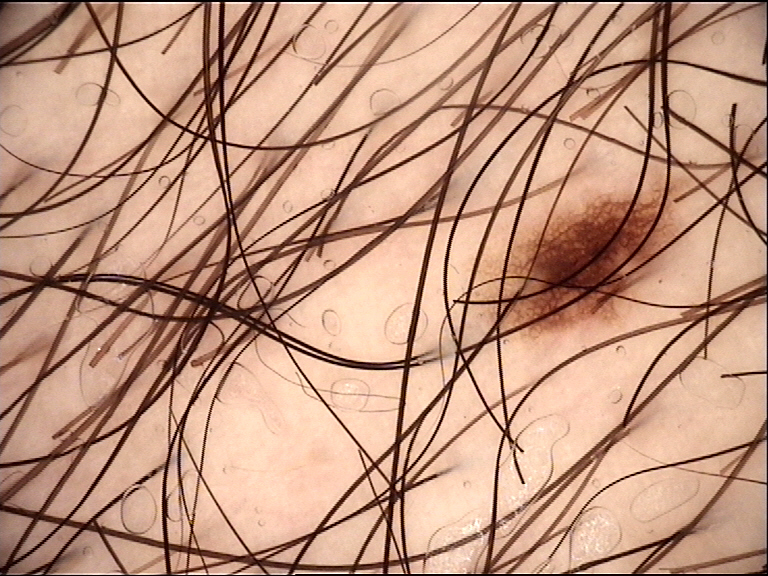A dermoscopic image of a skin lesion. Consistent with a benign lesion — a dysplastic junctional nevus.